The patient indicates the condition has been present for three to twelve months; the patient considered this a rash; the patient is 50–59, female; an image taken at an angle; symptoms reported: itching and burning; the patient indicates the lesion is raised or bumpy and fluid-filled; skin tone: Fitzpatrick V; located on the arm: 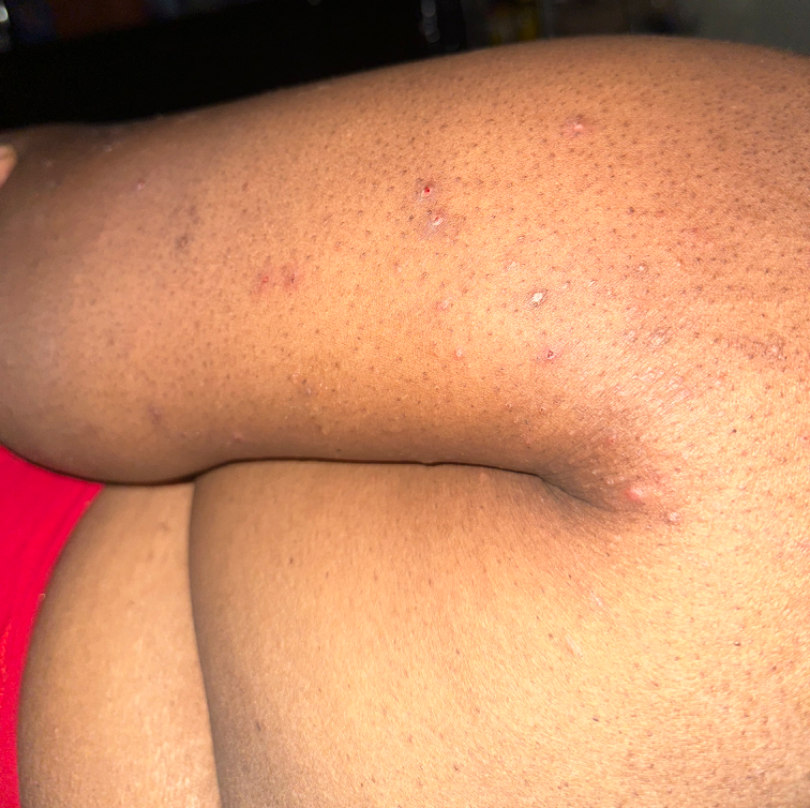assessment = reviewed remotely by one dermatologist: the leading impression is Prurigo nodularis; possibly Eczema.